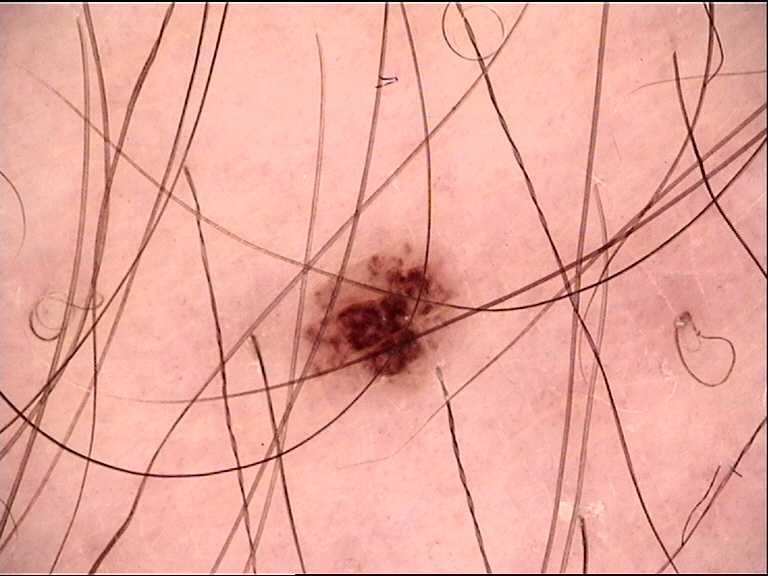class = dysplastic junctional nevus (expert consensus).